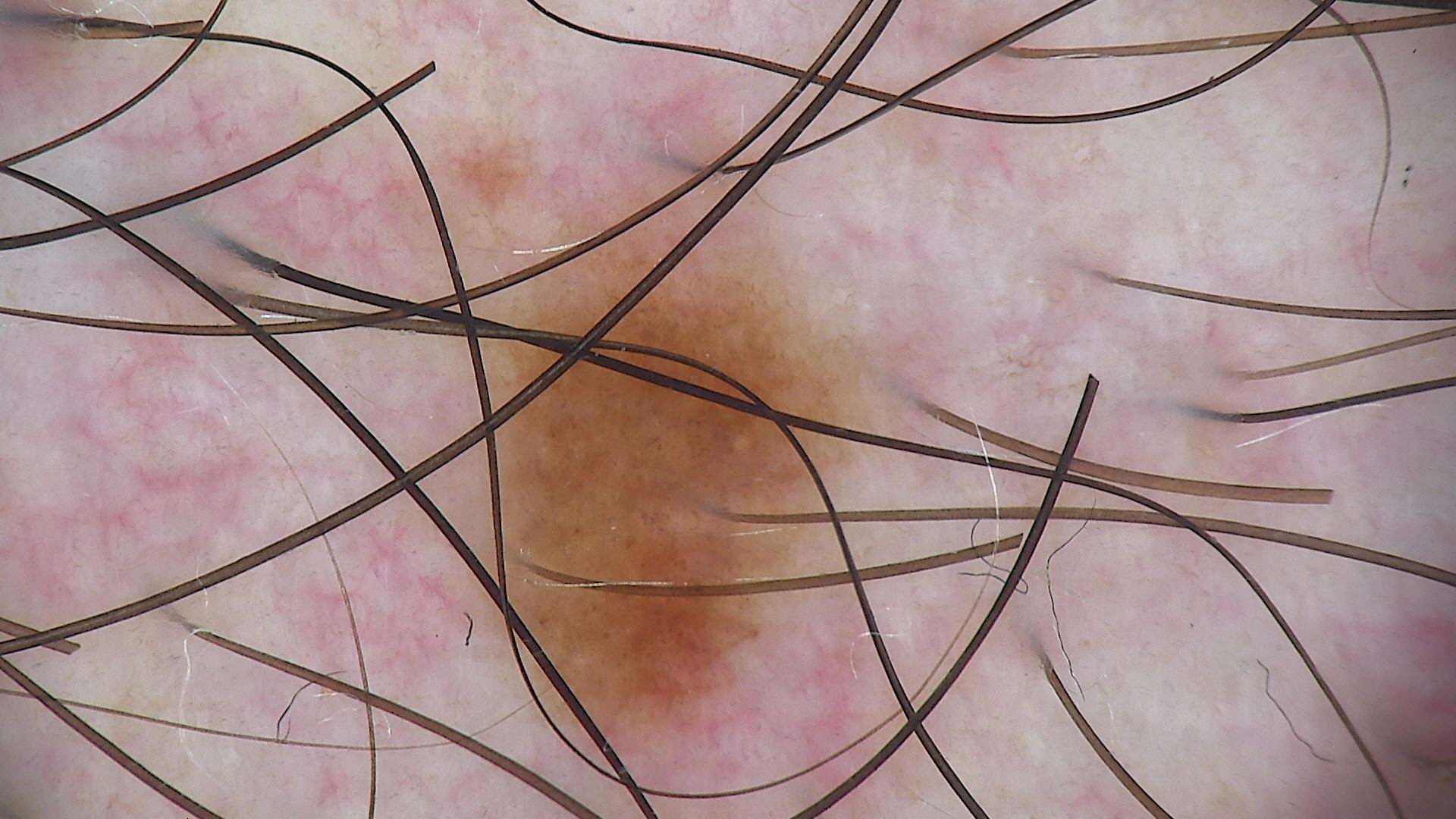The diagnosis was a dysplastic junctional nevus.